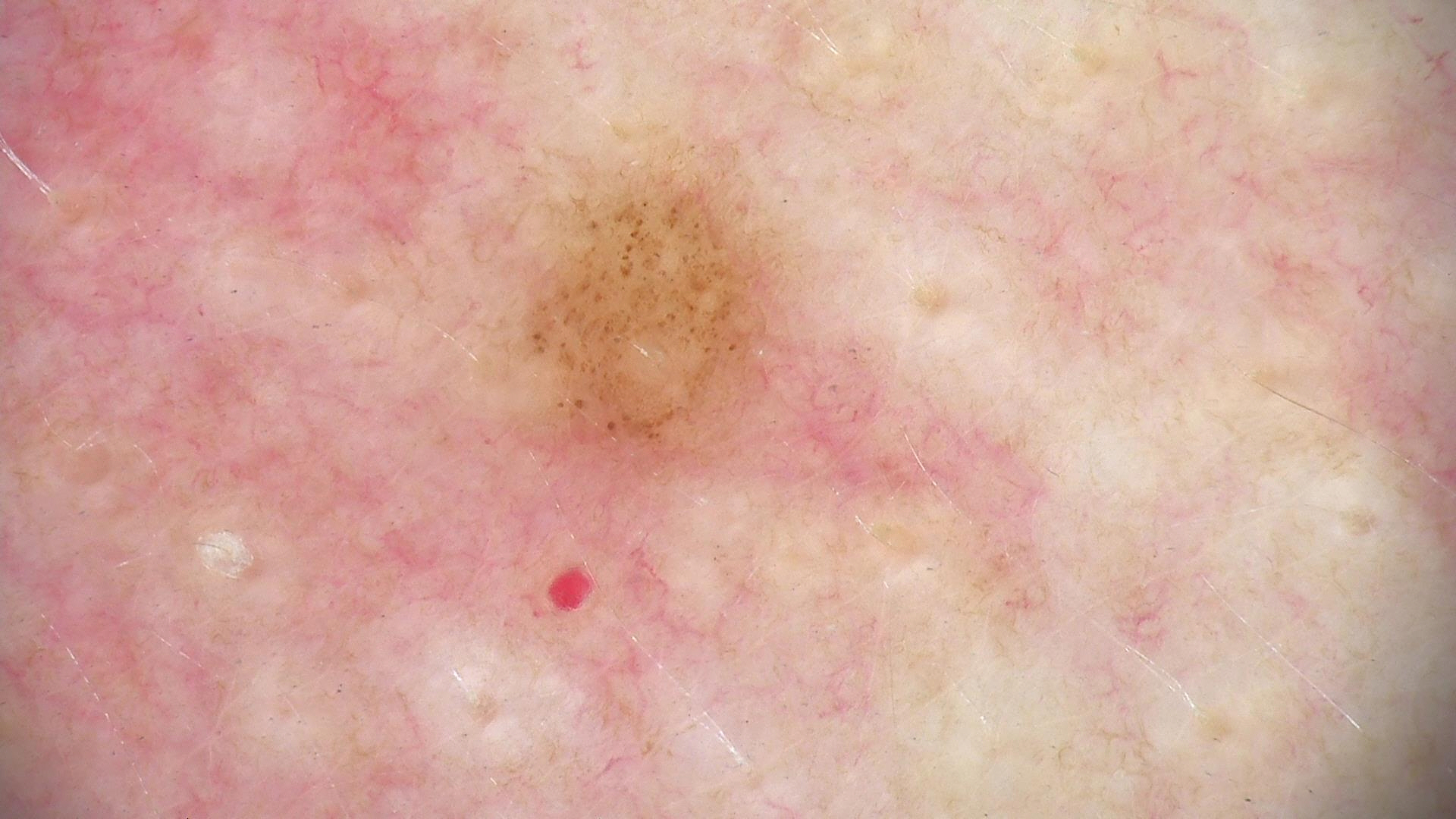  diagnosis:
    name: dysplastic junctional nevus
    code: jd
    malignancy: benign
    super_class: melanocytic
    confirmation: expert consensus